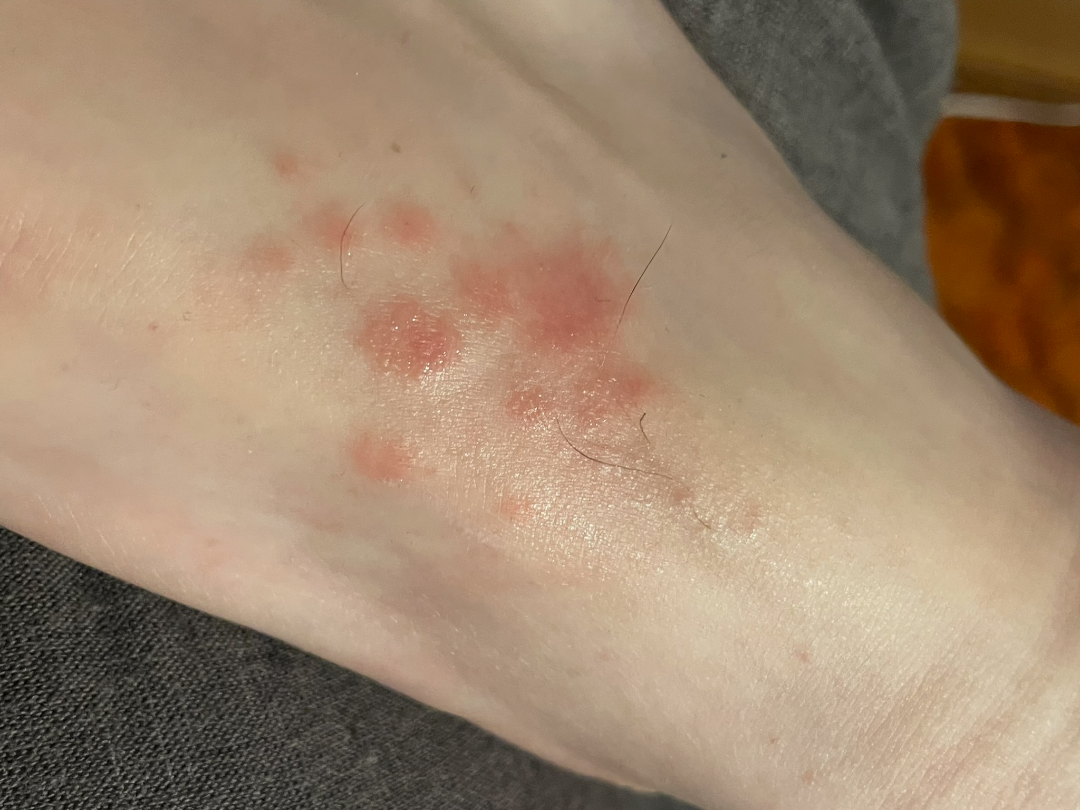Notes:
- patient: male, age 18–29
- location: top or side of the foot
- framing: close-up
- differential: the impression was split between Eczema, Allergic Contact Dermatitis and Irritant Contact Dermatitis